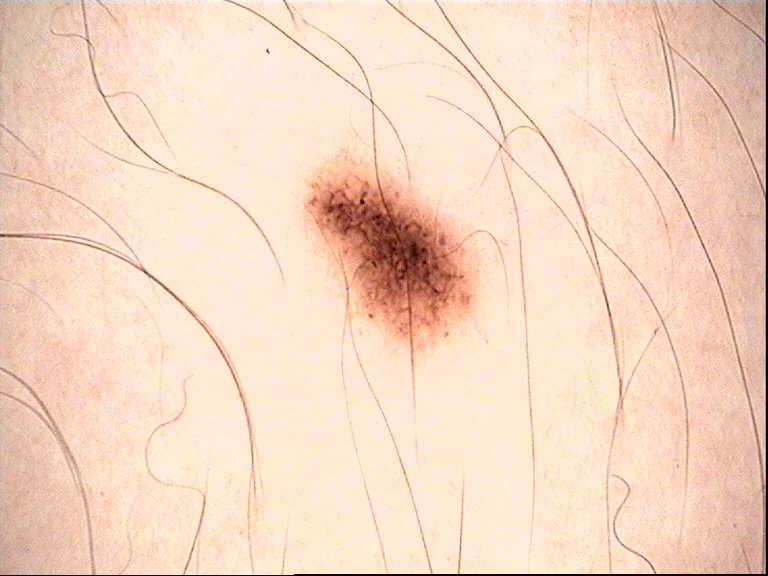diagnosis: dysplastic junctional nevus (expert consensus).